A skin lesion imaged with a dermatoscope:
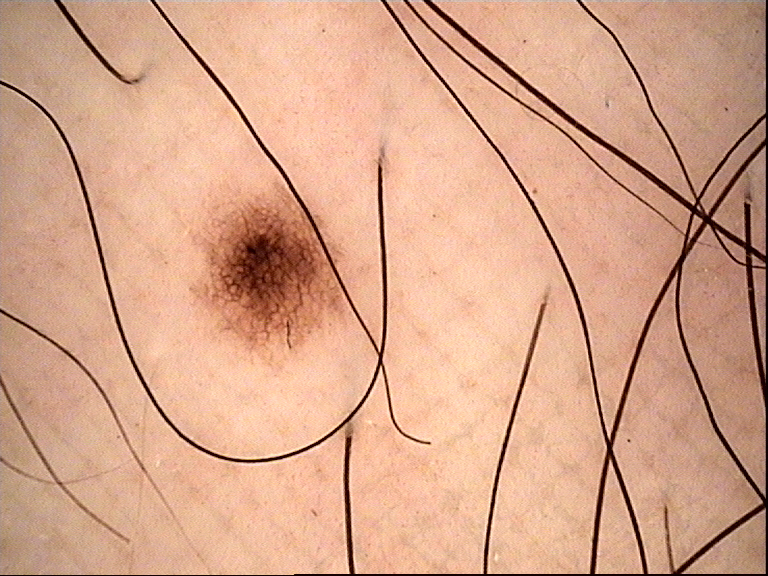category = banal; diagnostic label = junctional nevus (expert consensus).